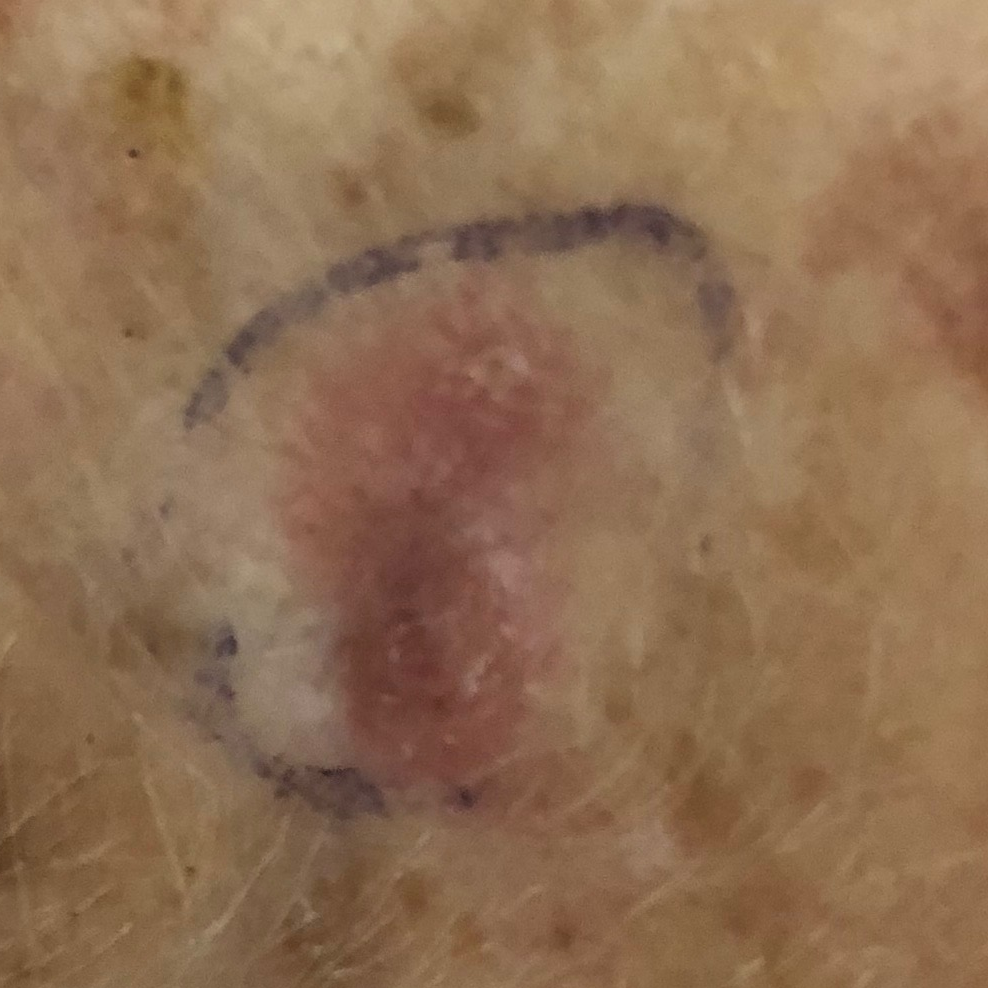{"skin_type": "II", "risk_factors": {"positive": ["prior skin cancer (patient or family)"]}, "patient": {"age": 66, "gender": "female"}, "lesion_size": {"diameter_1_mm": 17.0, "diameter_2_mm": 9.0}, "diagnosis": {"name": "basal cell carcinoma", "code": "BCC", "malignancy": "malignant", "confirmation": "histopathology"}}